A dermoscopic close-up of a skin lesion.
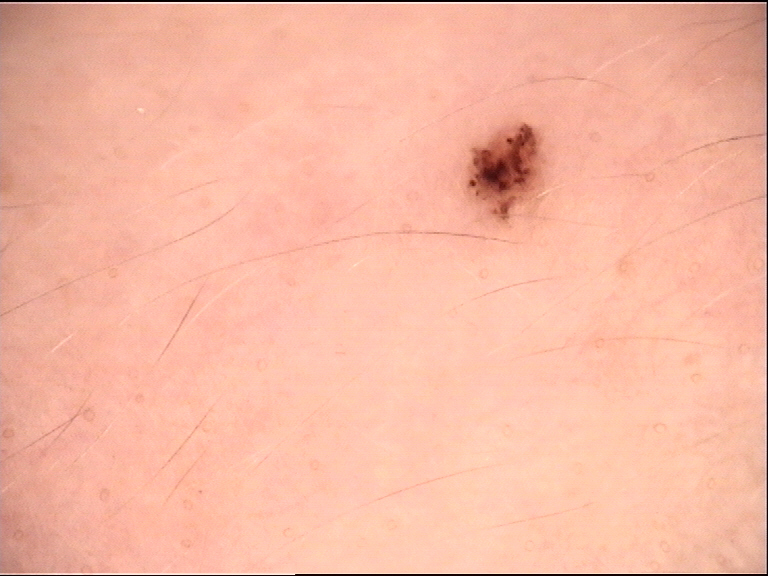Classified as a dysplastic junctional nevus.